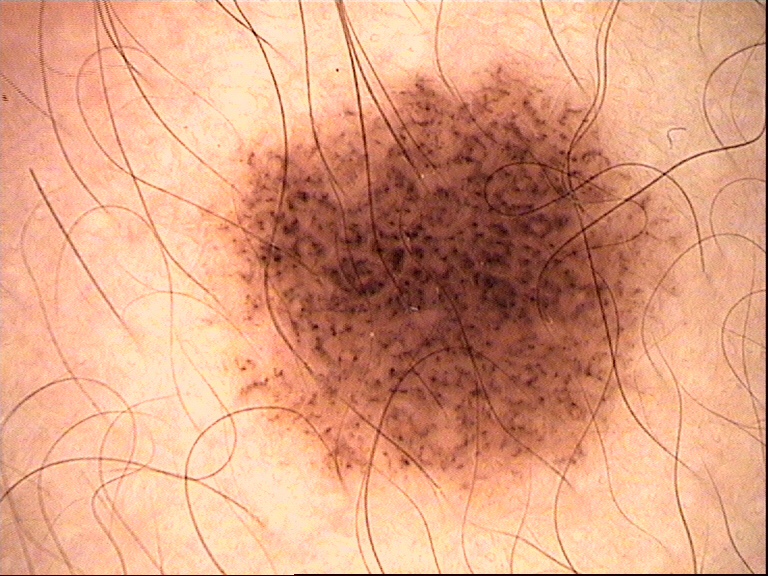Q: What is the diagnosis?
A: dysplastic junctional nevus (expert consensus)